Skin tone: FST II; lay graders estimated 2 on the Monk Skin Tone · the top or side of the foot and sole of the foot are involved · an image taken at a distance · reported lesion symptoms include bleeding, bothersome appearance and itching · reported duration is one to three months · the patient is 18–29, female.
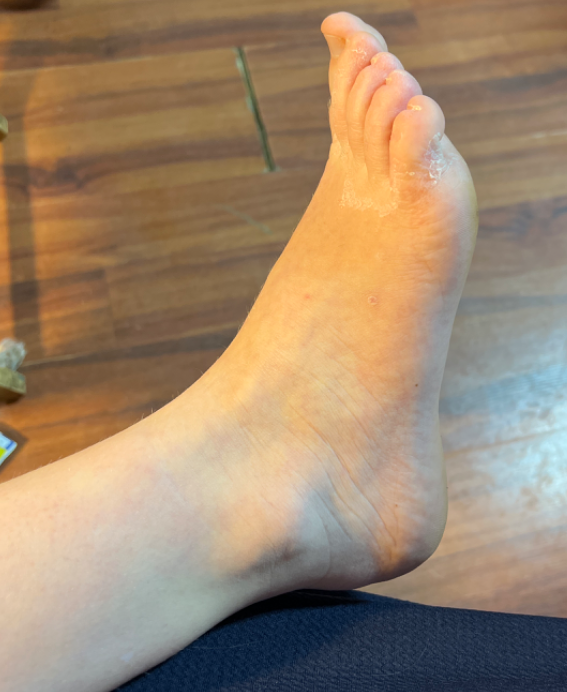Impression: Favoring Tinea; less likely is Eczema; less probable is Allergic Contact Dermatitis.